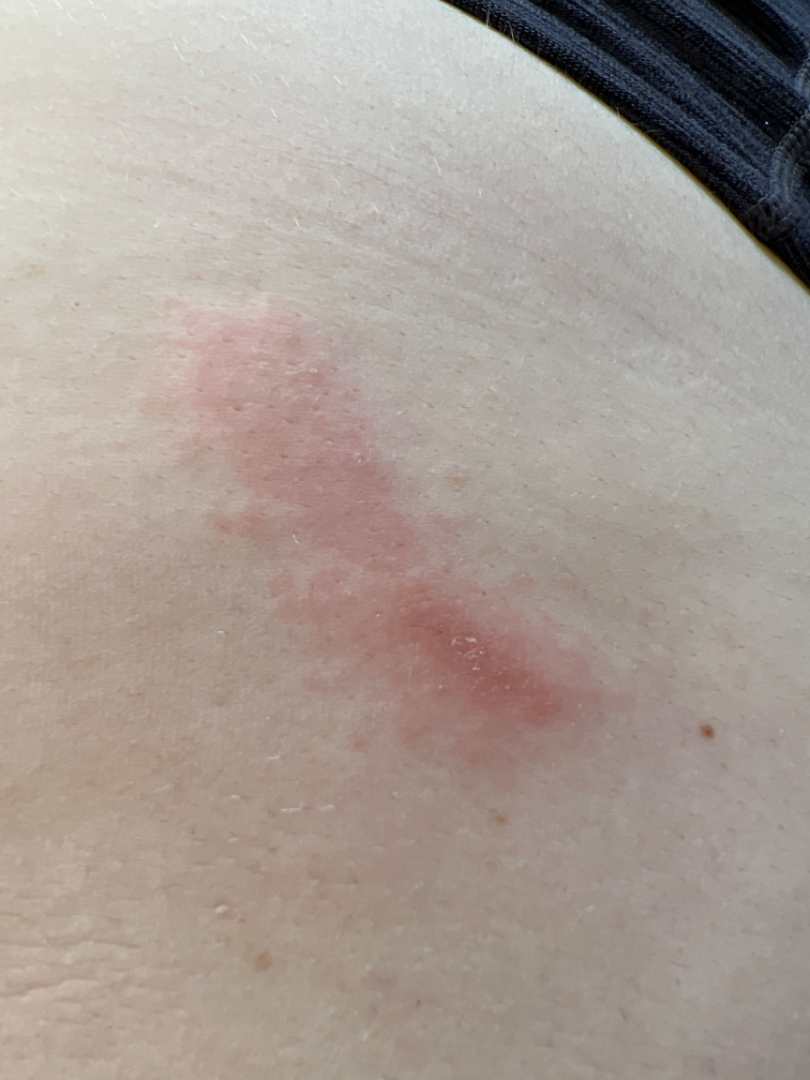{"body_site": "front of the torso", "patient_category": "a rash", "duration": "one to four weeks", "patient": "female, age 30–39", "shot_type": "close-up", "skin_tone": {"fitzpatrick": "I"}, "symptoms": ["enlargement", "itching"], "texture": ["raised or bumpy", "rough or flaky"], "differential": {"leading": ["Allergic Contact Dermatitis"], "considered": ["Contact dermatitis"], "unlikely": ["Acute dermatitis, NOS", "Irritant Contact Dermatitis", "Urticaria"]}}